A dermoscopic photograph of a skin lesion.
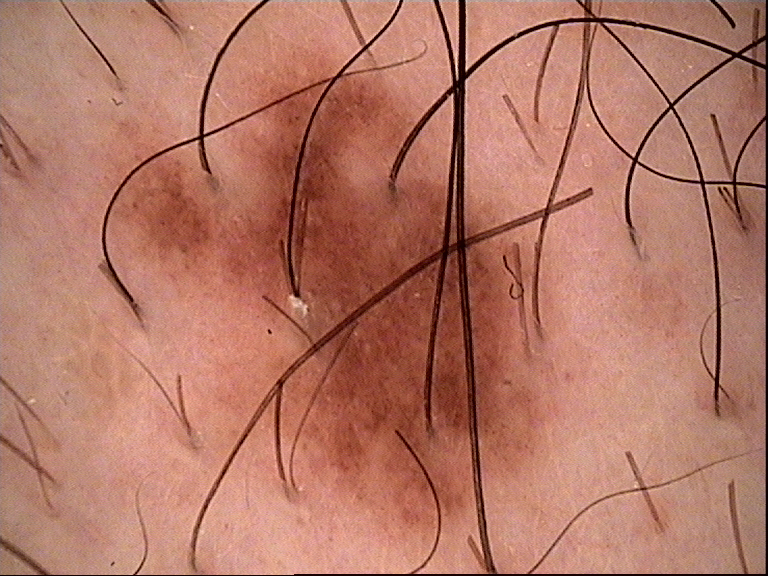Labeled as a benign lesion — a dysplastic junctional nevus.